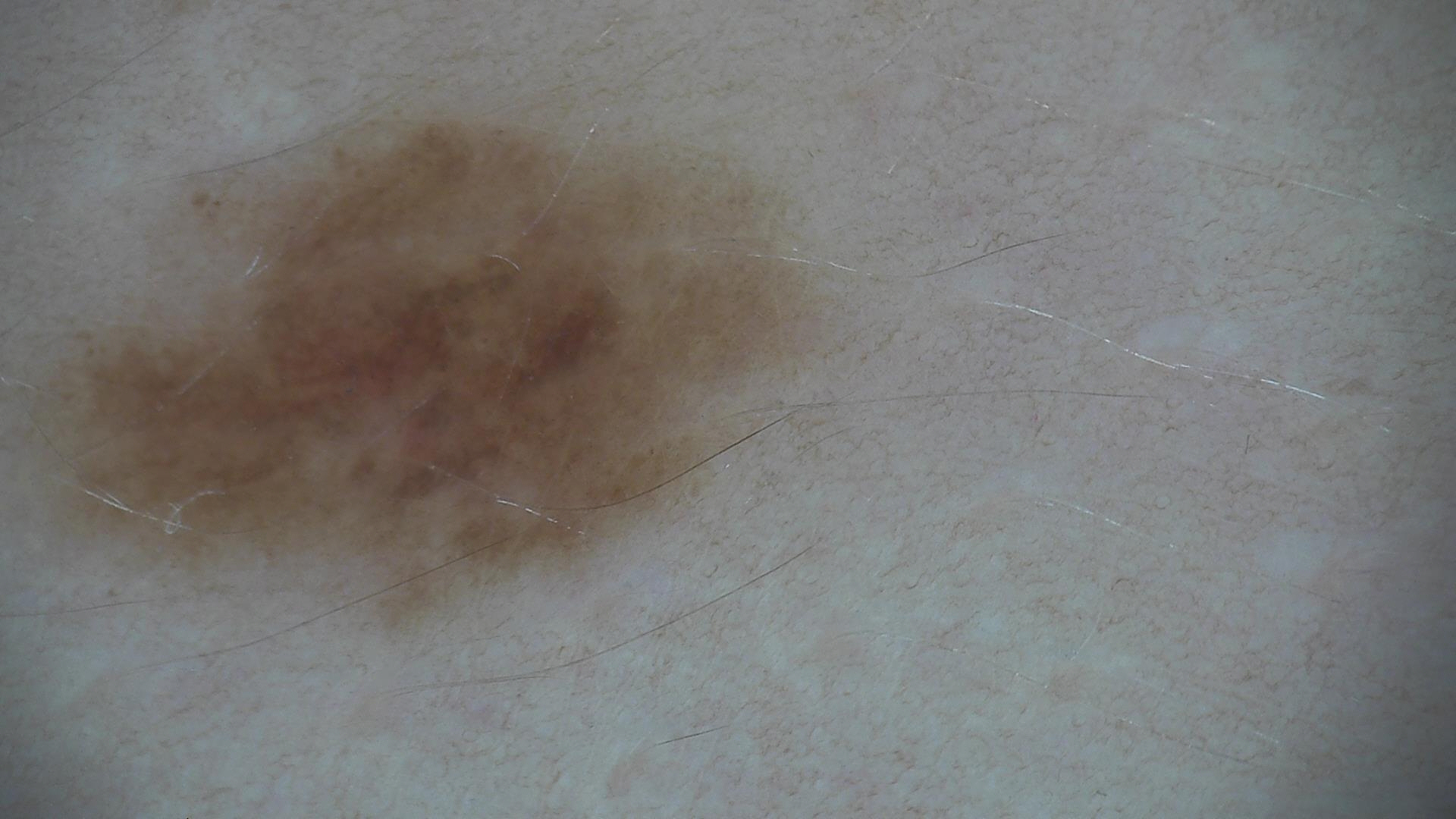assessment: dysplastic junctional nevus (expert consensus).